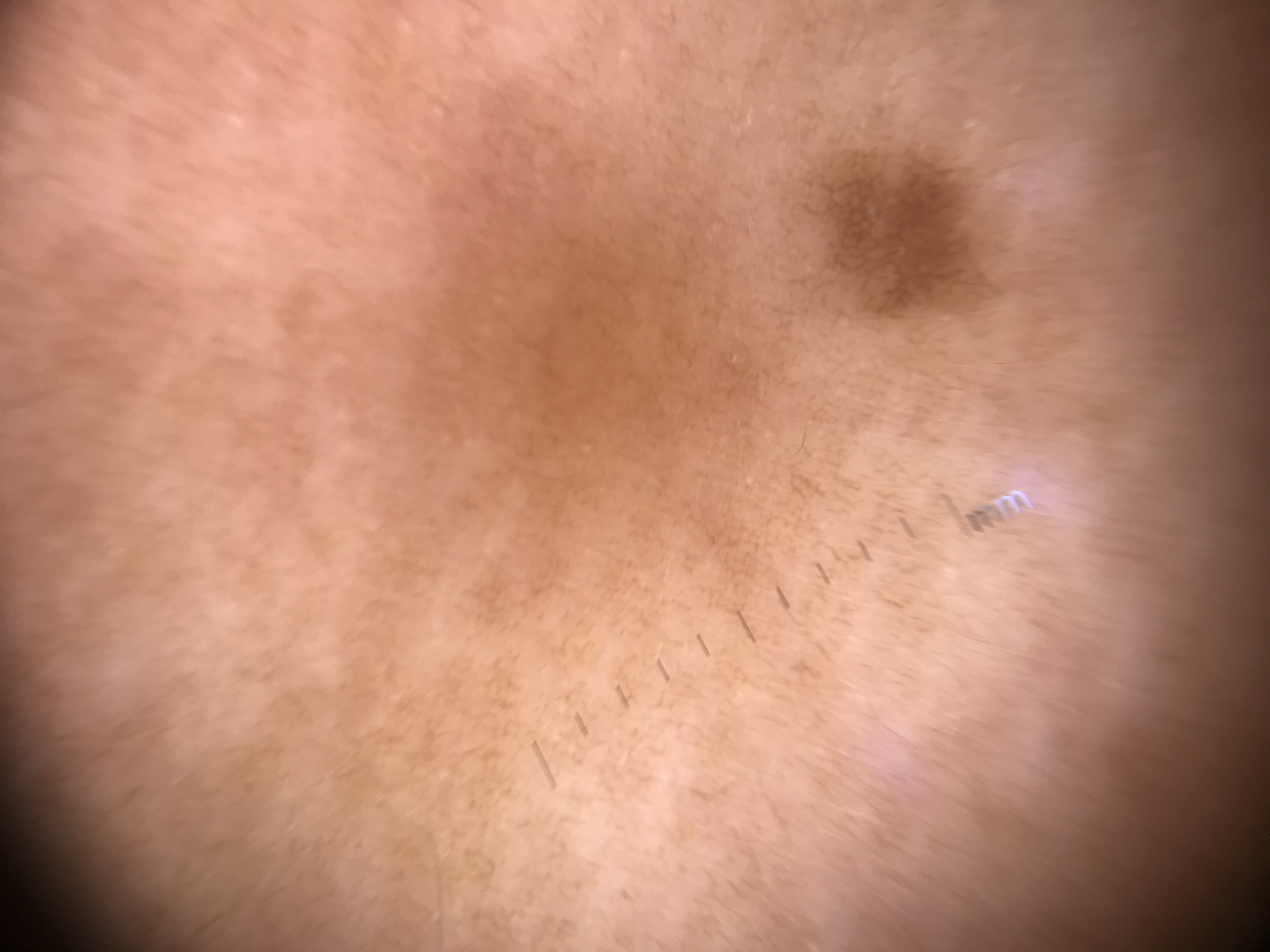Impression: Labeled as a lentigo simplex.